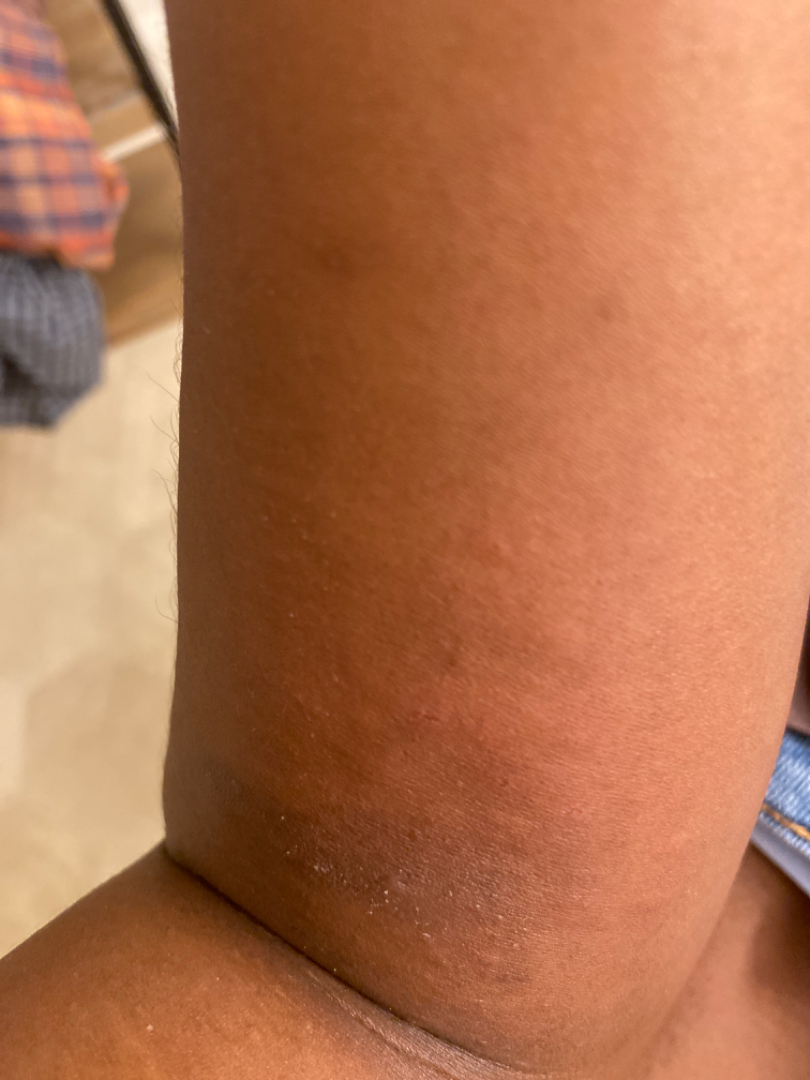On independent review by the dermatologists, the favored diagnosis is Eczema; less probable is Scabies; a remote consideration is Allergic Contact Dermatitis; less likely is Tinea; a more distant consideration is Psoriasis.